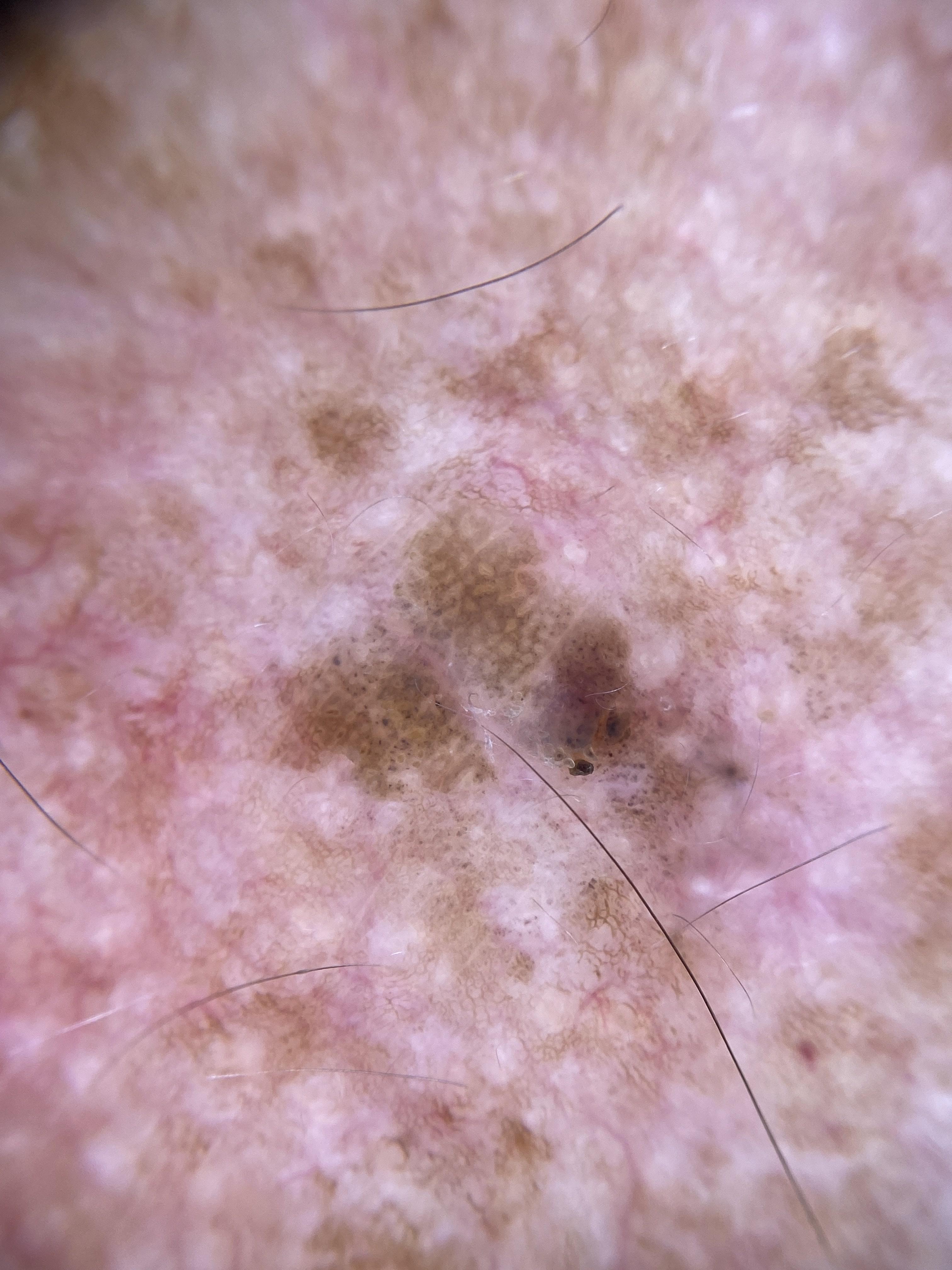* modality · dermoscopic image
* FST · II
* site · an upper extremity
* diagnosis · Seborrheic keratosis (biopsy-proven)